A female patient age 67; on a questionnaire the patient reported a personal history of skin cancer; a dermatoscopic image of a skin lesion — 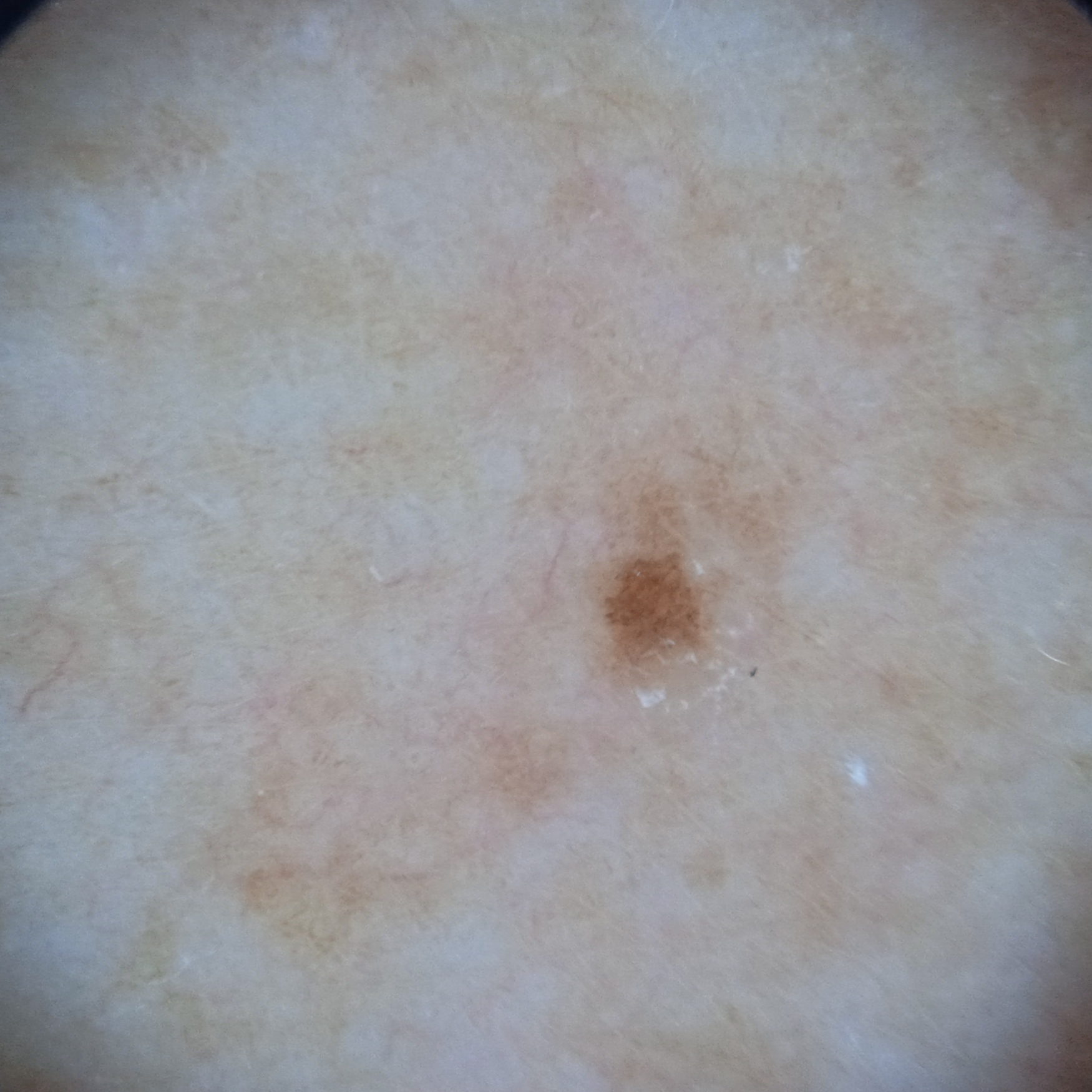The lesion measures approximately 1.3 mm. The consensus diagnosis for this lesion was a melanocytic nevus.